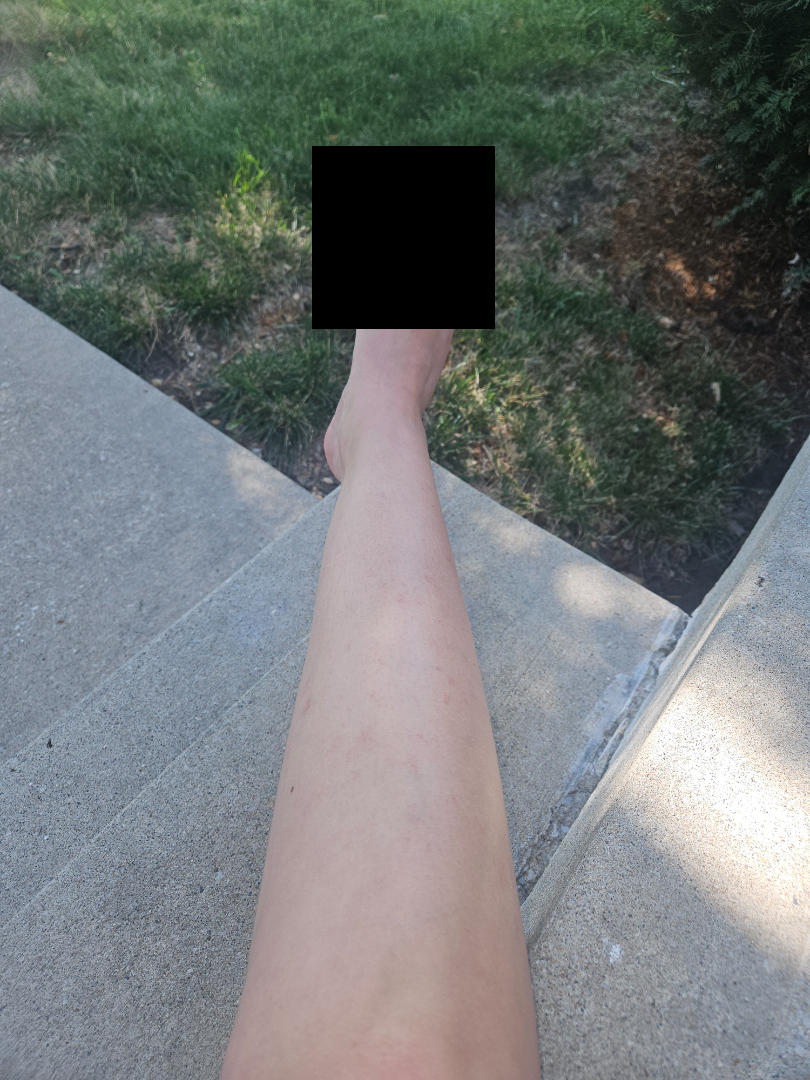Q: Could the case be diagnosed?
A: not assessable
Q: What is the affected area?
A: leg
Q: Image view?
A: at a distance